A dermoscopic close-up of a skin lesion: 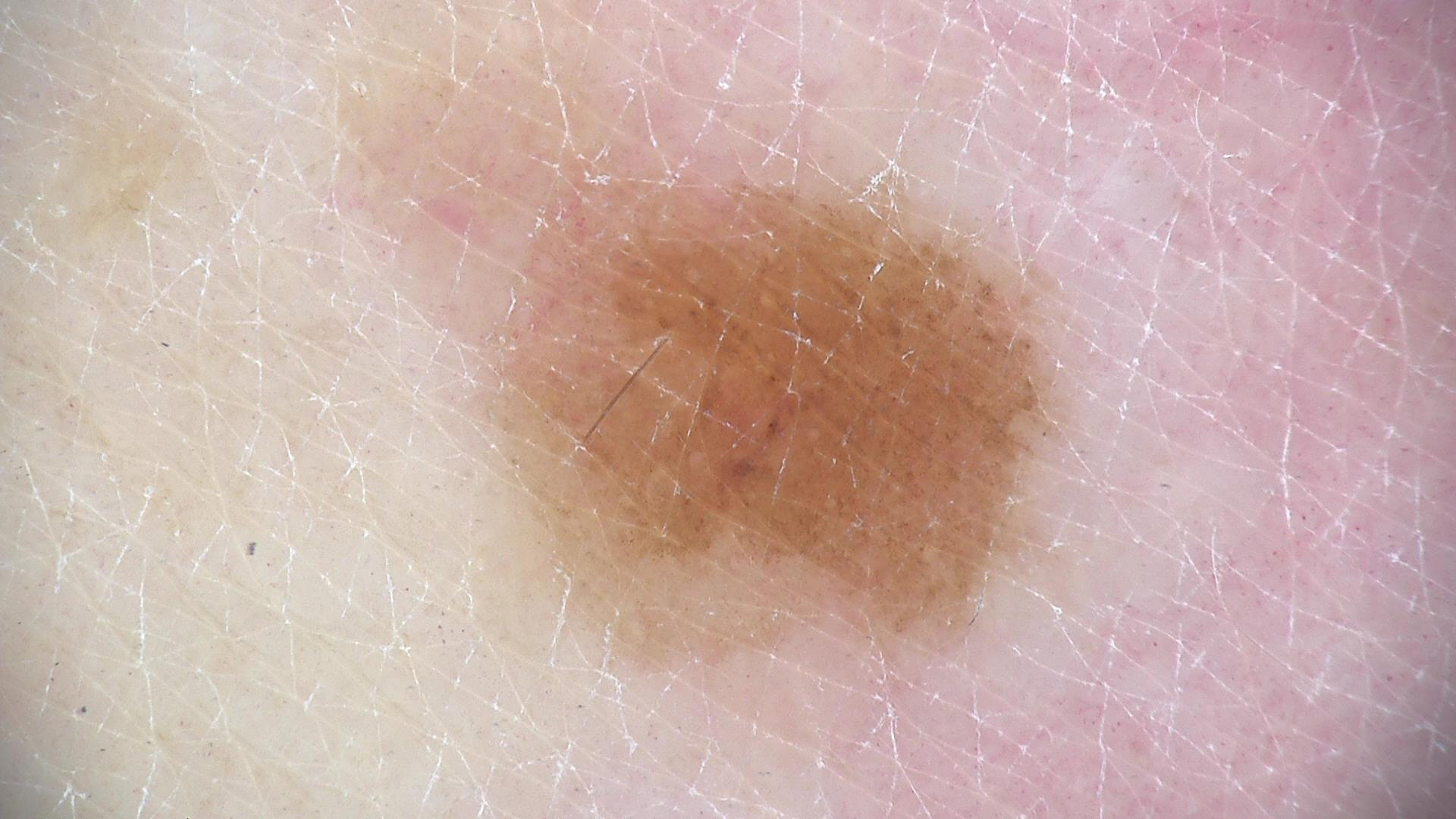diagnostic label: dysplastic junctional nevus (expert consensus).